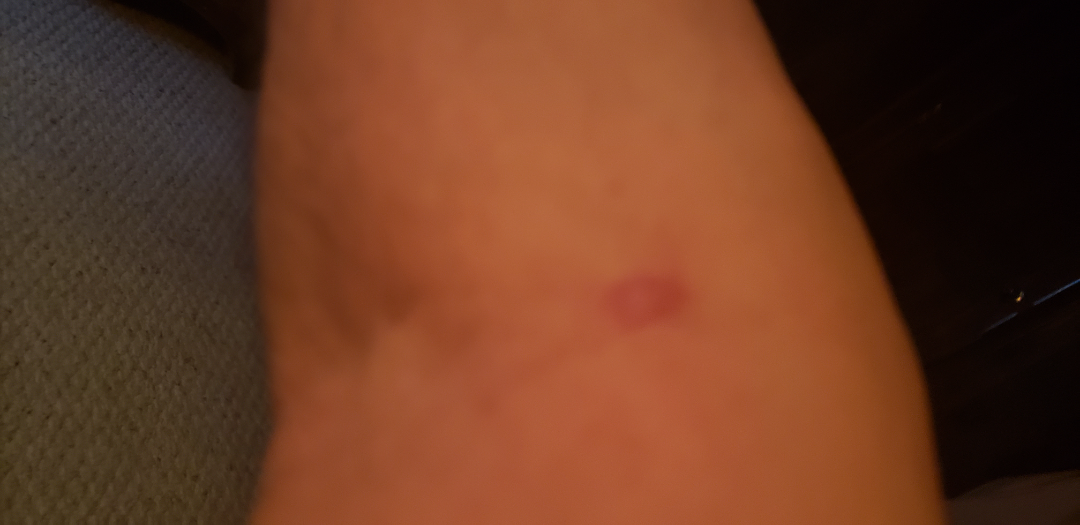| feature | finding |
|---|---|
| assessment | not assessable |
| lesion symptoms | itching |
| skin tone | Fitzpatrick phototype IV; lay graders estimated MST 2 or 4 |
| subject | male, age 50–59 |
| duration | one to four weeks |
| view | close-up |
| texture | raised or bumpy |
| body site | arm |